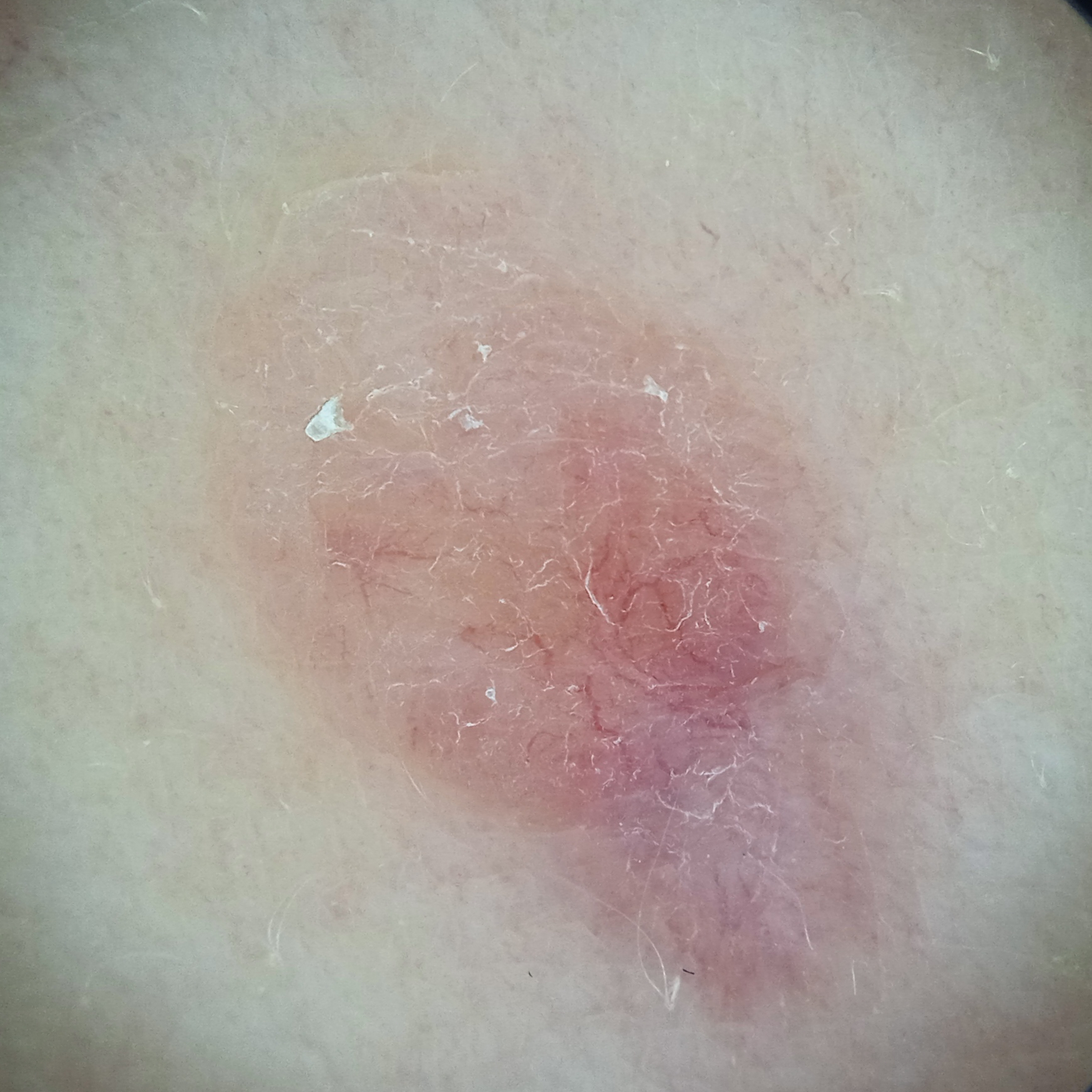Few moles overall by the patient's own estimate.
Referred for assessment of suspected basal cell carcinoma.
The patient says their skin reddens painfully with sun exposure.
The lesion is on the back.
Measuring roughly 12.3 mm.
The biopsy diagnosis was a basal cell carcinoma, following excision, with a measured thickness of 1.1 mm.